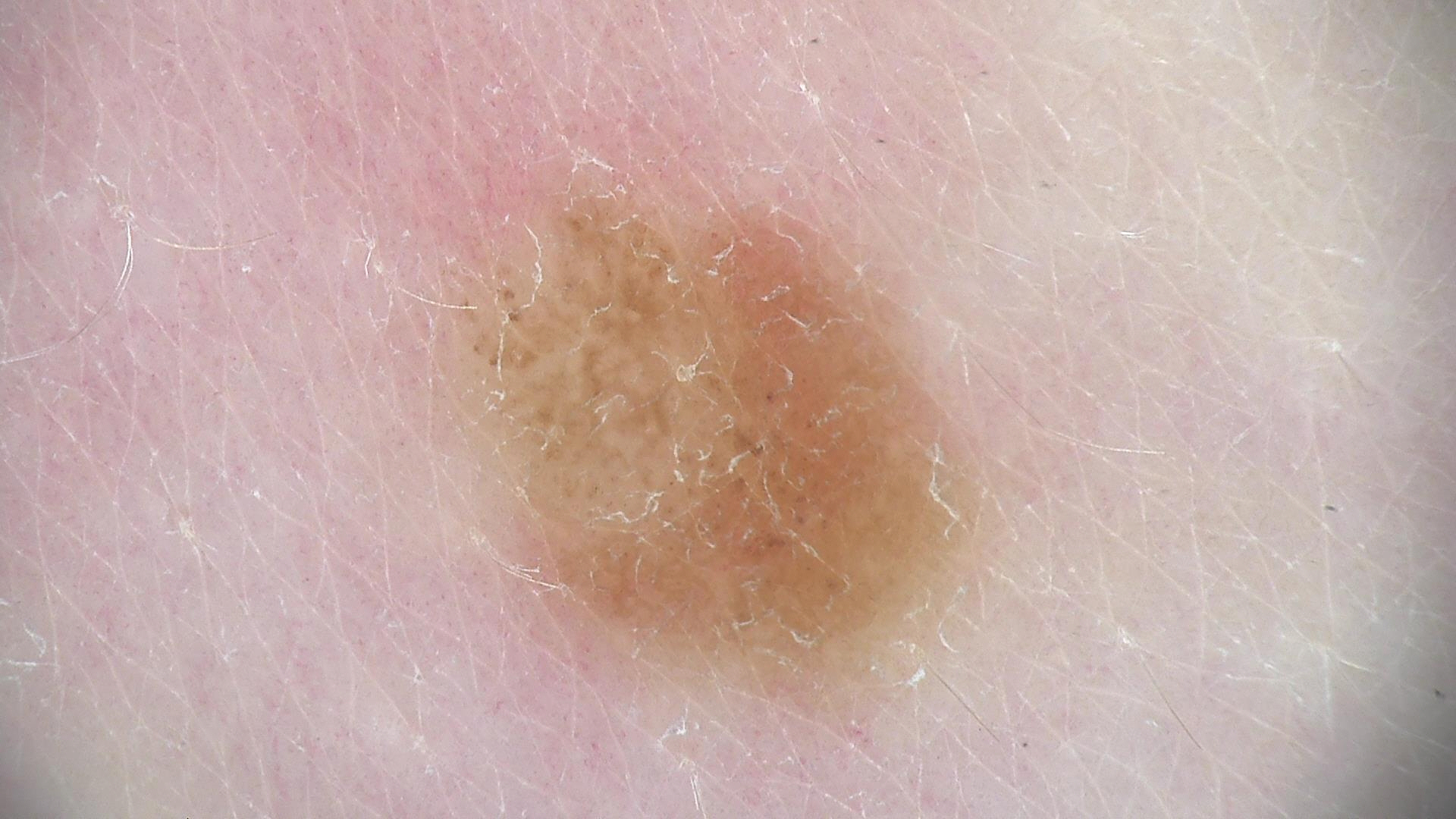The morphology is that of a banal lesion. The diagnostic label was a compound nevus.